Dermoscopy of a skin lesion. A male patient, about 50 years old:
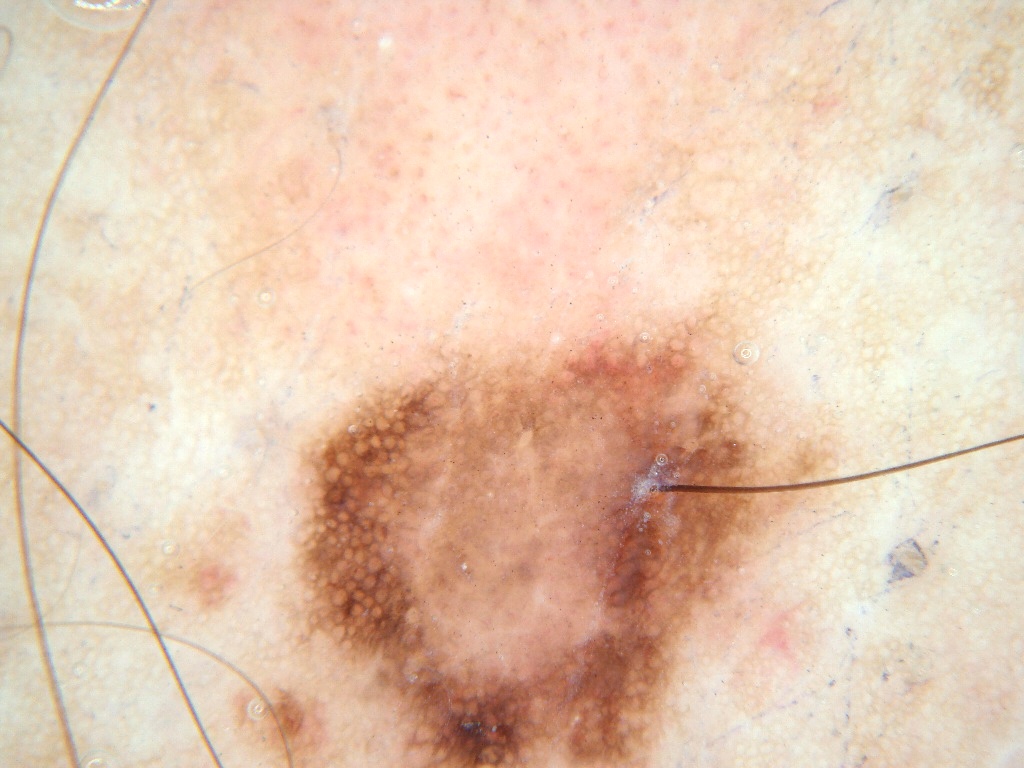The lesion is bounded by <bbox>268, 298, 815, 766</bbox>. Dermoscopic review identifies milia-like cysts, globules, and pigment network; no negative network or streaks. Clinically diagnosed as a melanocytic nevus.